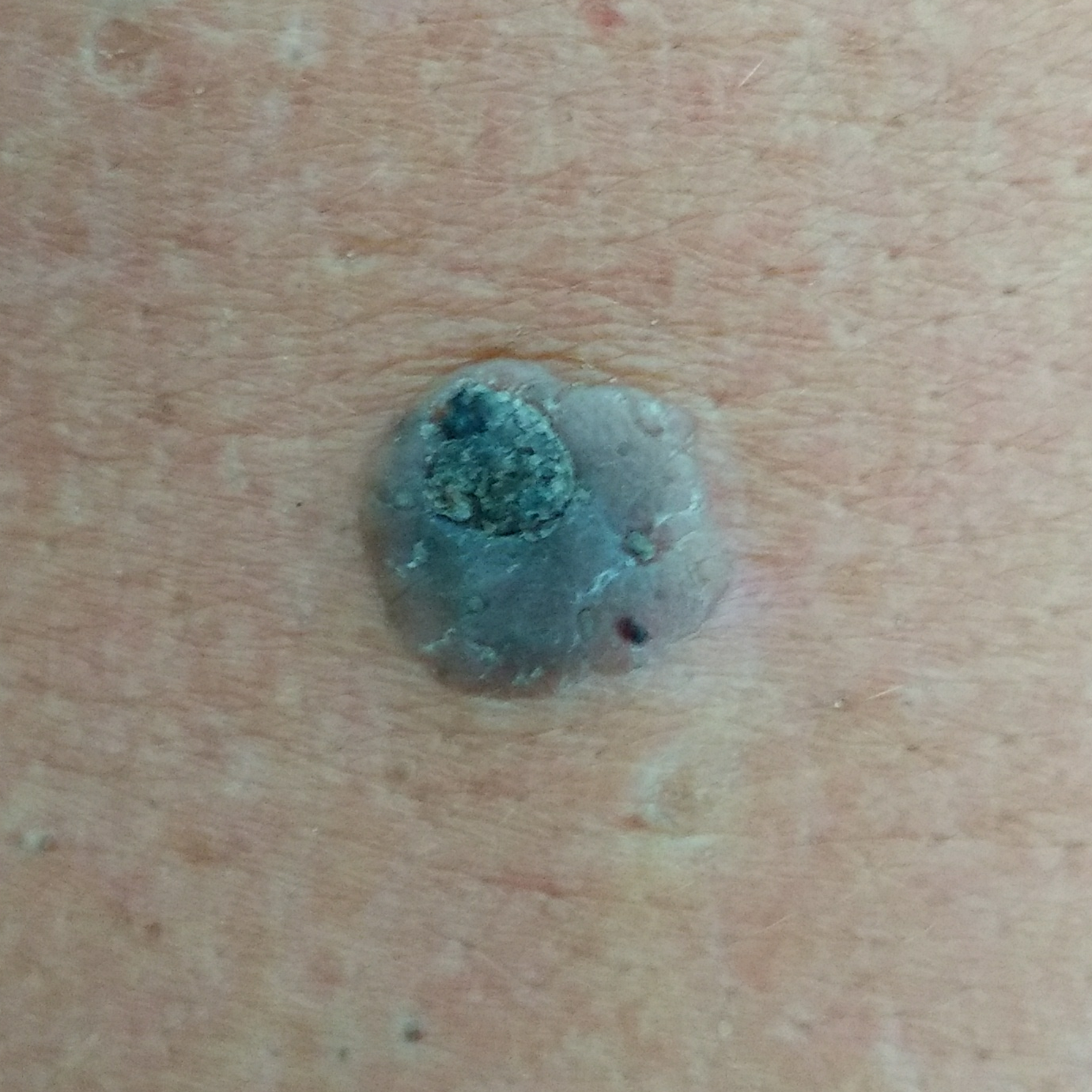The lesion was found on the back. The diagnostic impression was a seborrheic keratosis.